The leg is involved; the subject is 40–49, female; close-up view — 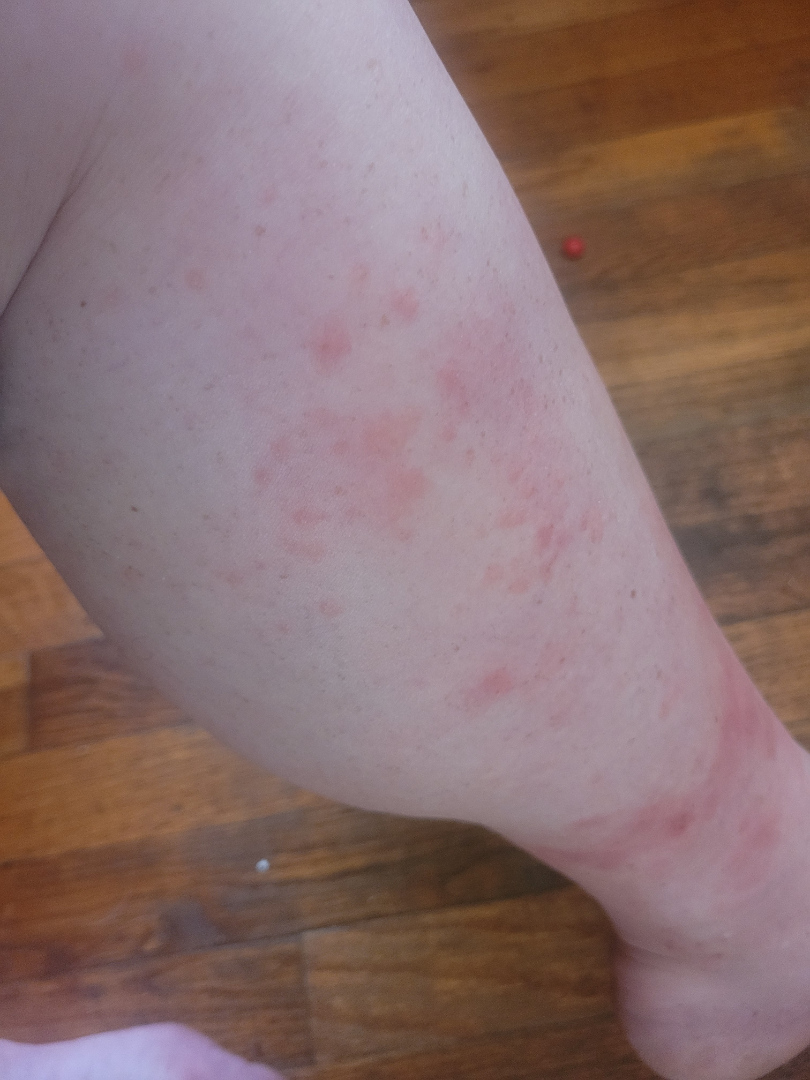The differential includes Stasis Dermatitis, Eczema and Allergic Contact Dermatitis, with no clear leading consideration.